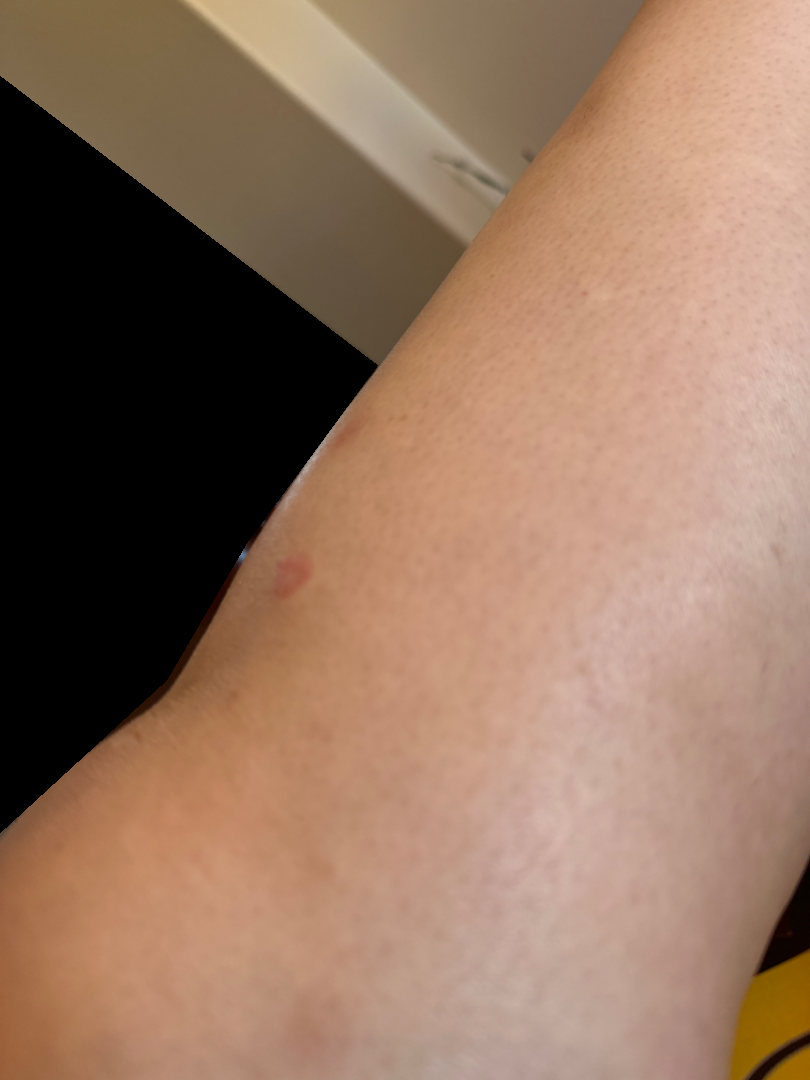On remote dermatologist review, the favored diagnosis is Allergic Contact Dermatitis; also raised was Eczema.